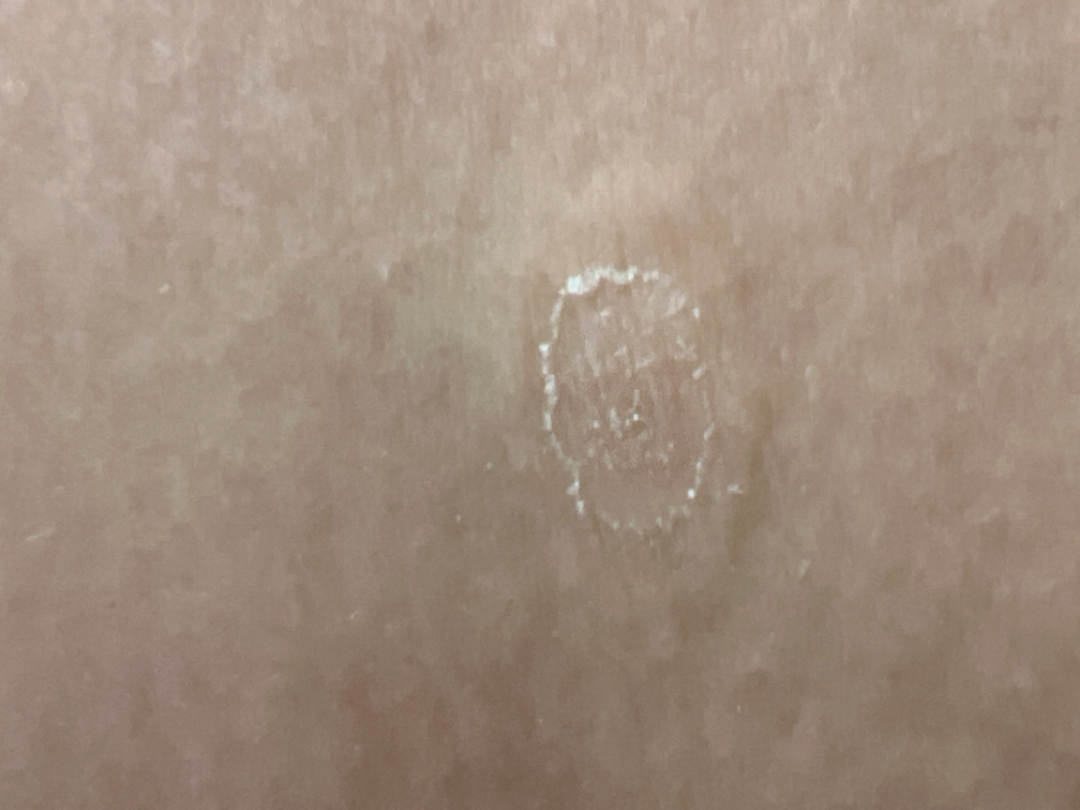Close-up view. One reviewing dermatologist: the impression was split between Porokeratosis, Xerosis and Keratosis.